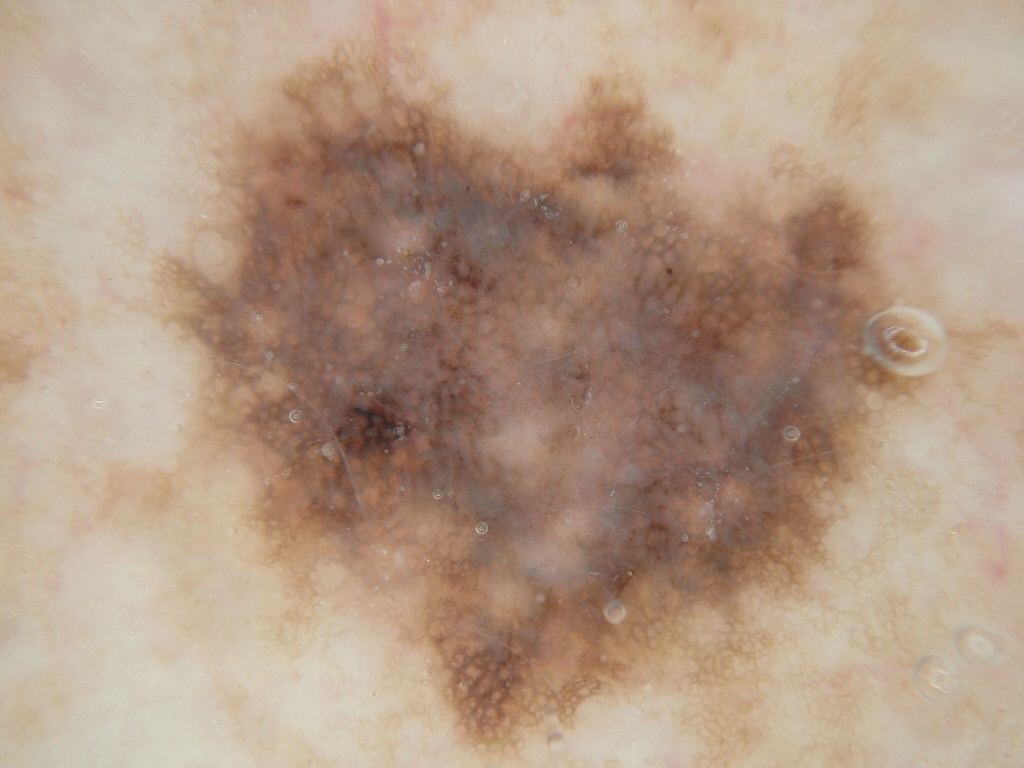<lesion>
  <image>
    <modality>dermoscopy</modality>
  </image>
  <patient>
    <sex>male</sex>
    <age_approx>65</age_approx>
  </patient>
  <lesion_location>
    <bbox_xyxy>160, 56, 930, 743</bbox_xyxy>
  </lesion_location>
  <dermoscopic_features>
    <present>pigment network</present>
    <absent>milia-like cysts, globules, negative network, streaks</absent>
  </dermoscopic_features>
  <lesion_extent>
    <approx_field_fraction_pct>42</approx_field_fraction_pct>
  </lesion_extent>
  <diagnosis>
    <name>melanoma</name>
    <malignancy>malignant</malignancy>
    <lineage>melanocytic</lineage>
    <provenance>histopathology</provenance>
  </diagnosis>
</lesion>